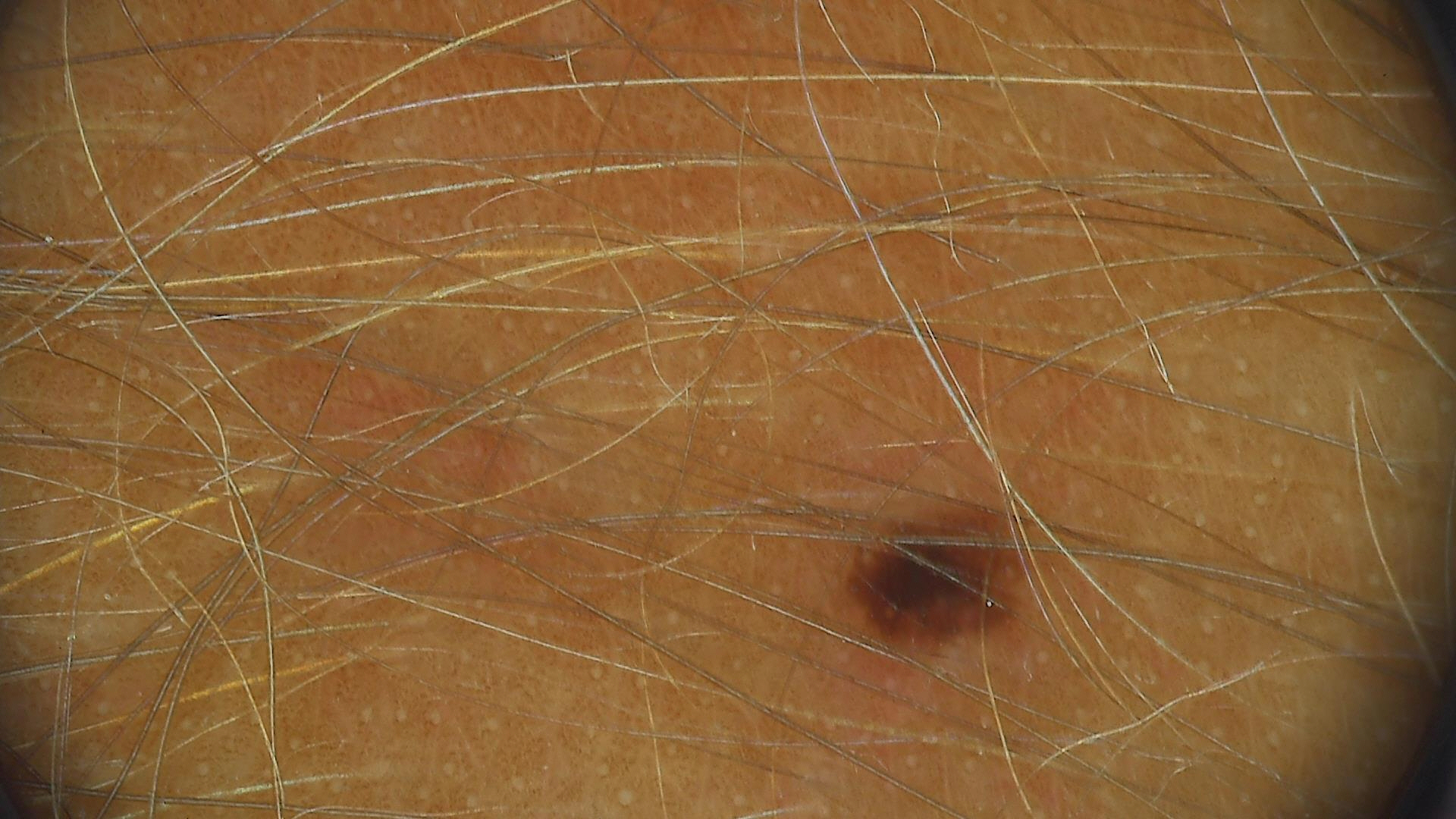<case>
  <image>dermatoscopy</image>
  <diagnosis>
    <name>junctional nevus</name>
    <code>jb</code>
    <malignancy>benign</malignancy>
    <super_class>melanocytic</super_class>
    <confirmation>expert consensus</confirmation>
  </diagnosis>
</case>